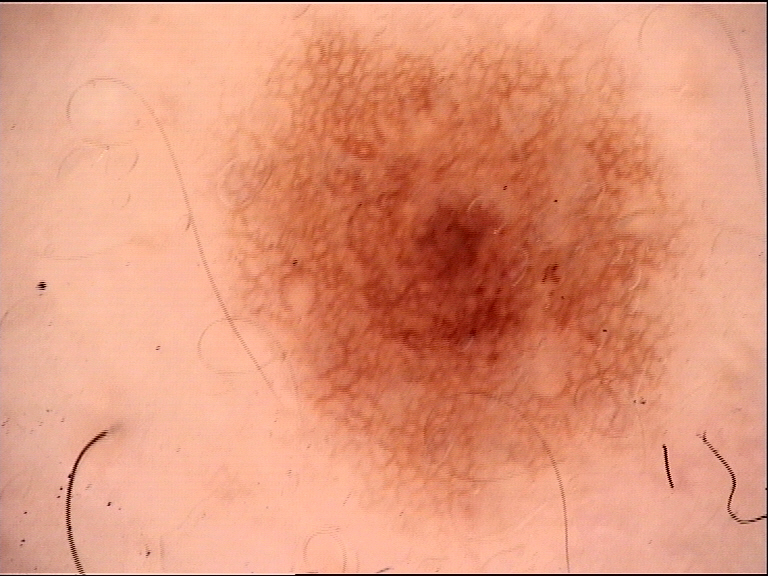A dermoscopic image of a skin lesion.
This is a banal lesion.
The diagnostic label was a junctional nevus.